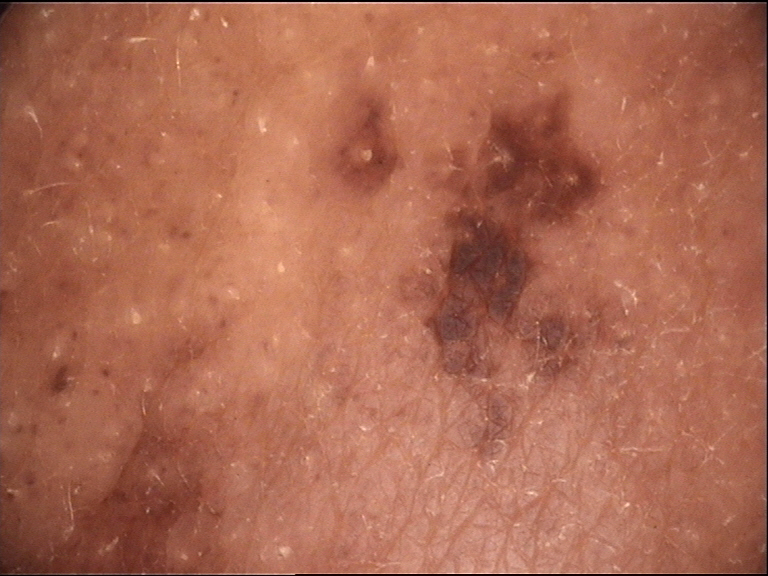A dermoscopic photograph of a skin lesion.
The diagnostic label was a congenital compound nevus.